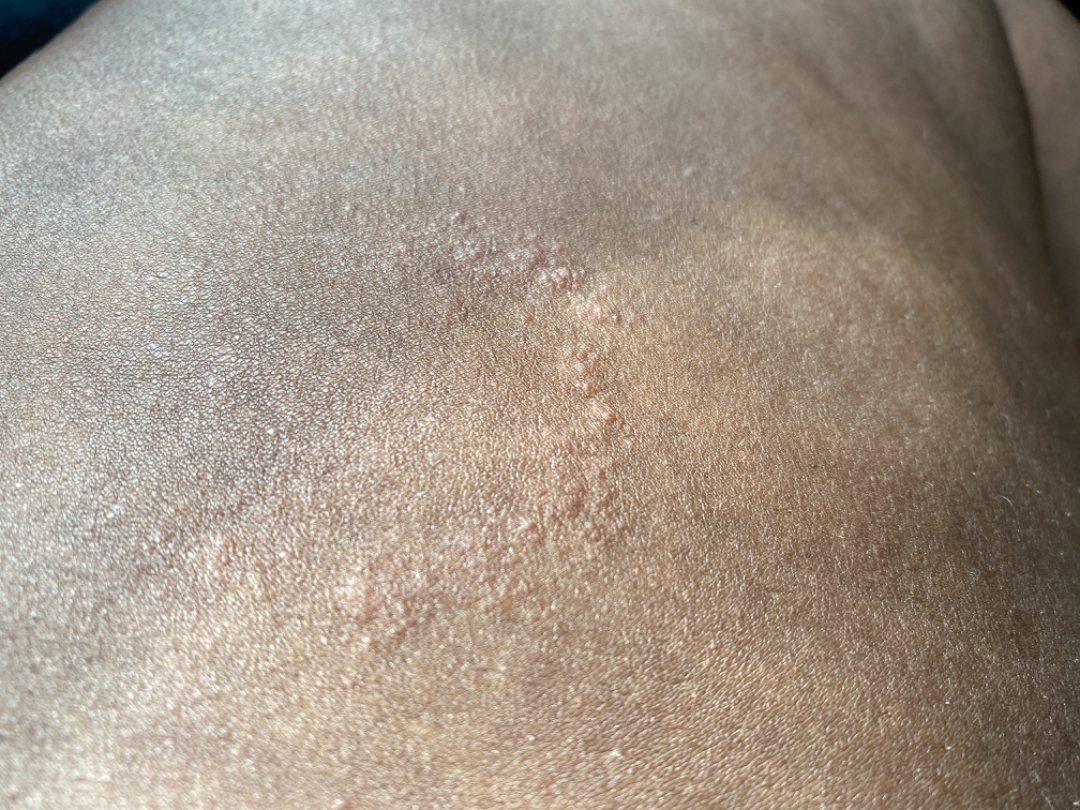Impression:
On teledermatology review, most consistent with Tinea.